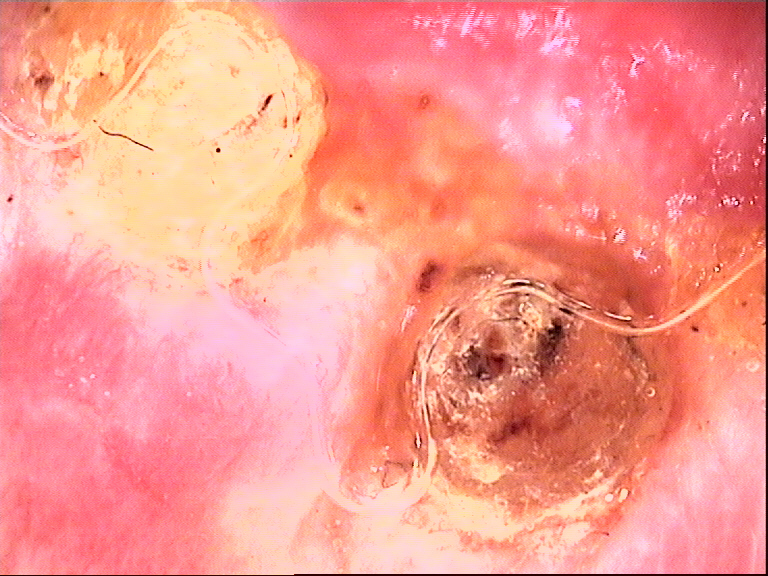Case: A skin lesion imaged with a dermatoscope. Pathology: Biopsy-confirmed as a keratinocytic lesion — a squamous cell carcinoma.